A clinical close-up photograph of a skin lesion; a subject age 47.
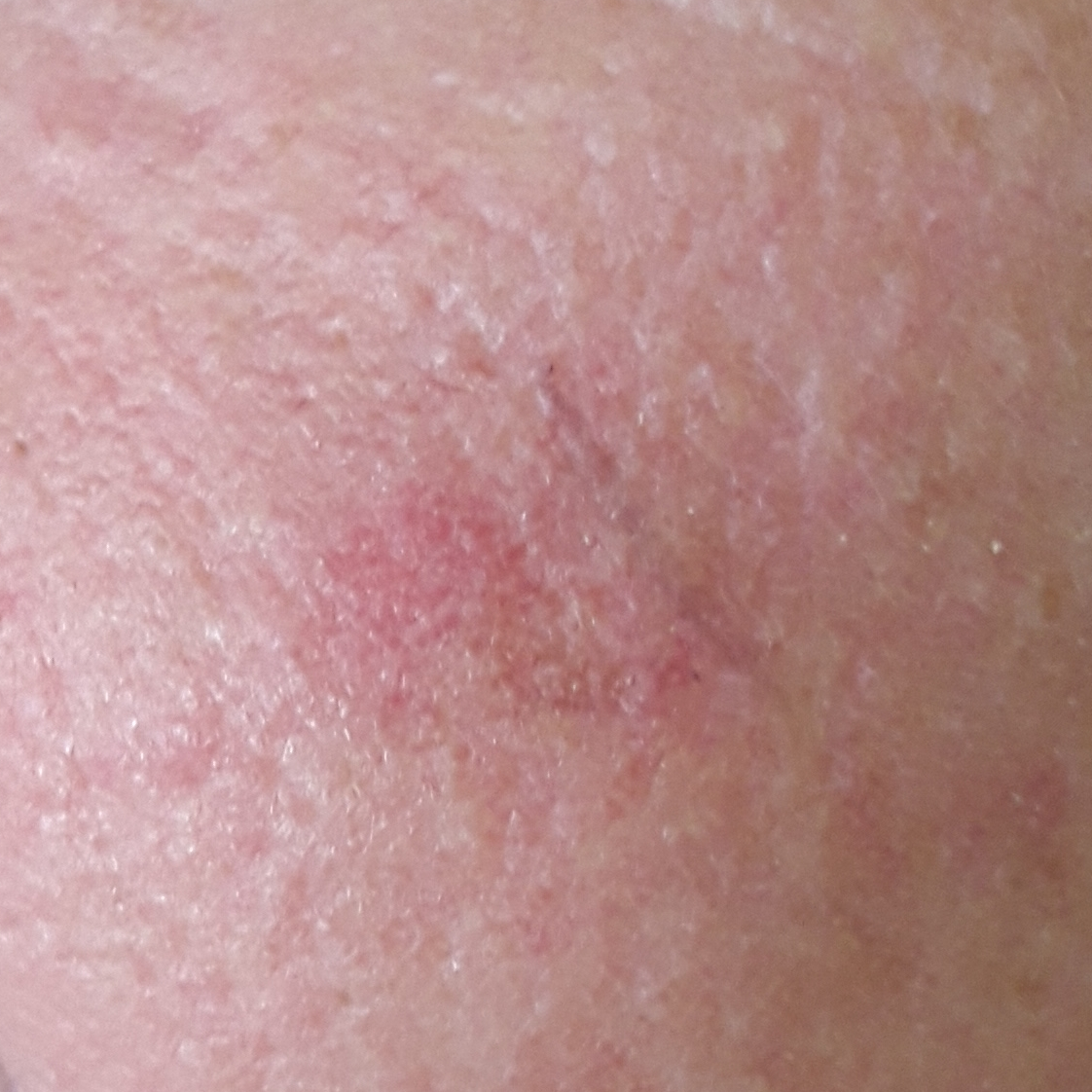Case summary:
Located on the face. The patient describes that the lesion has grown and hurts, but has not changed and has not bled.
Conclusion:
Expert review favored an actinic keratosis.